A dermoscopic photograph of a skin lesion.
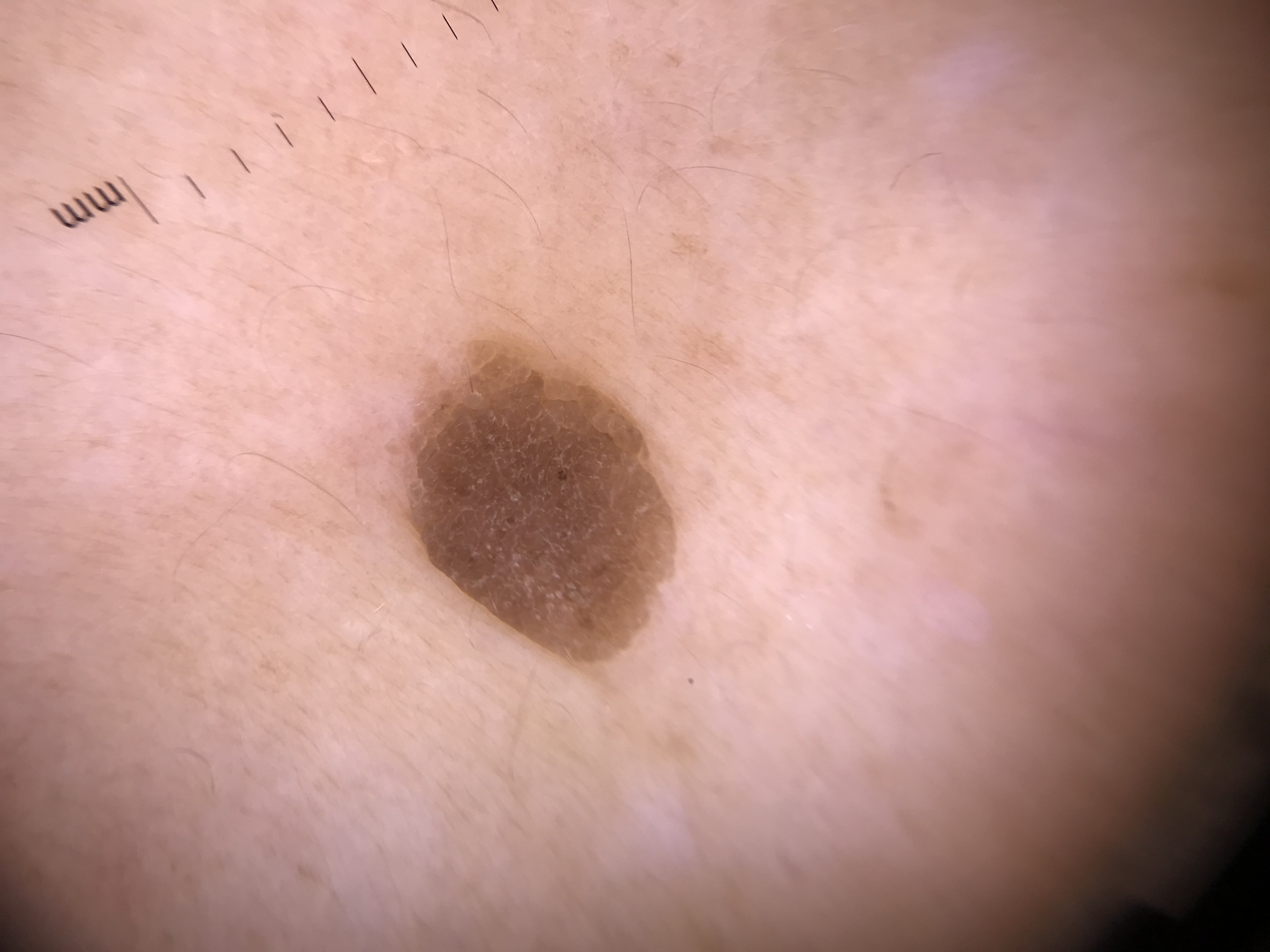lesion type: keratinocytic, diagnostic label: seborrheic keratosis (expert consensus).